This is a dermoscopic photograph of a skin lesion.
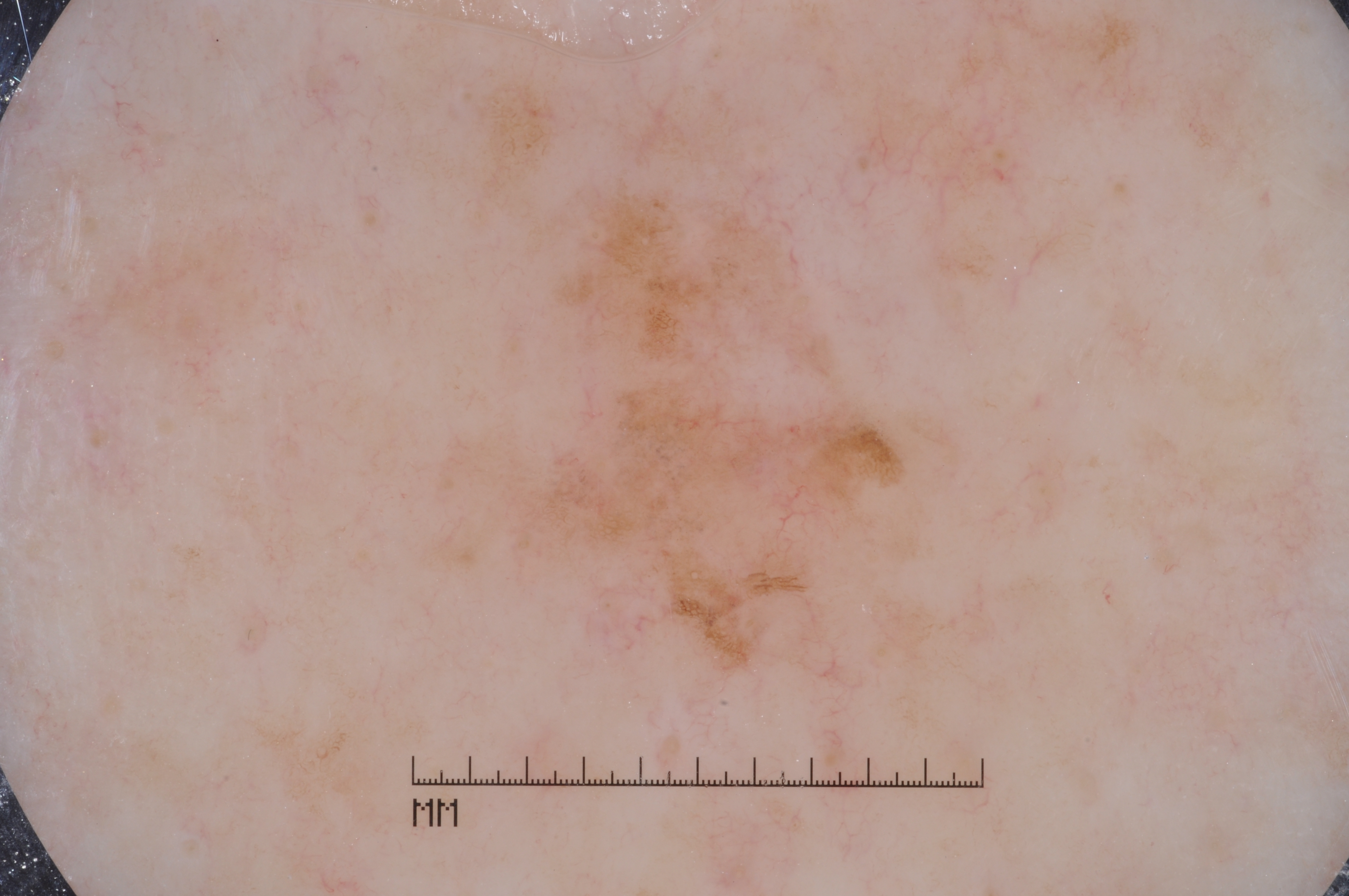Case summary:
The visible lesion spans <box>506, 196, 927, 665</box>.
Pathology:
The biopsy diagnosis was a melanoma.